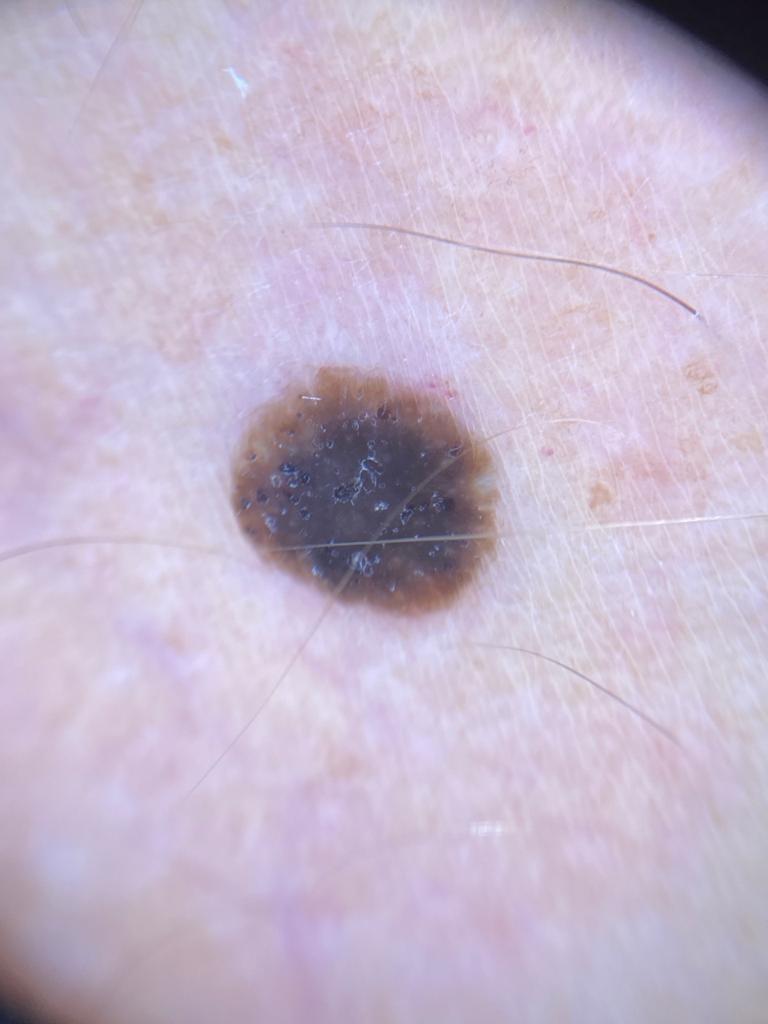Q: What is the patient's skin type?
A: II
Q: What is the anatomic site?
A: the trunk, specifically the posterior trunk
Q: What is this lesion?
A: Seborrheic keratosis